A skin lesion imaged with a dermatoscope.
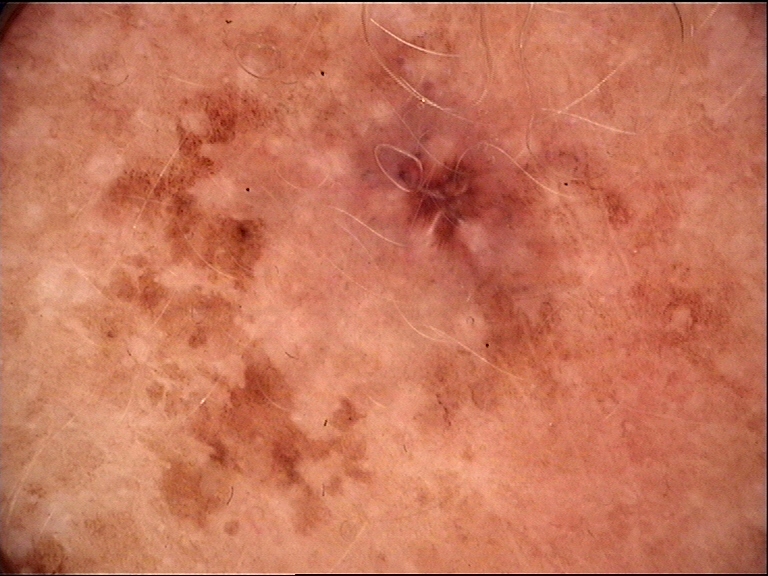class — dysplastic junctional nevus (expert consensus).